Close-up view. The affected area is the front of the torso and arm. The patient is female — 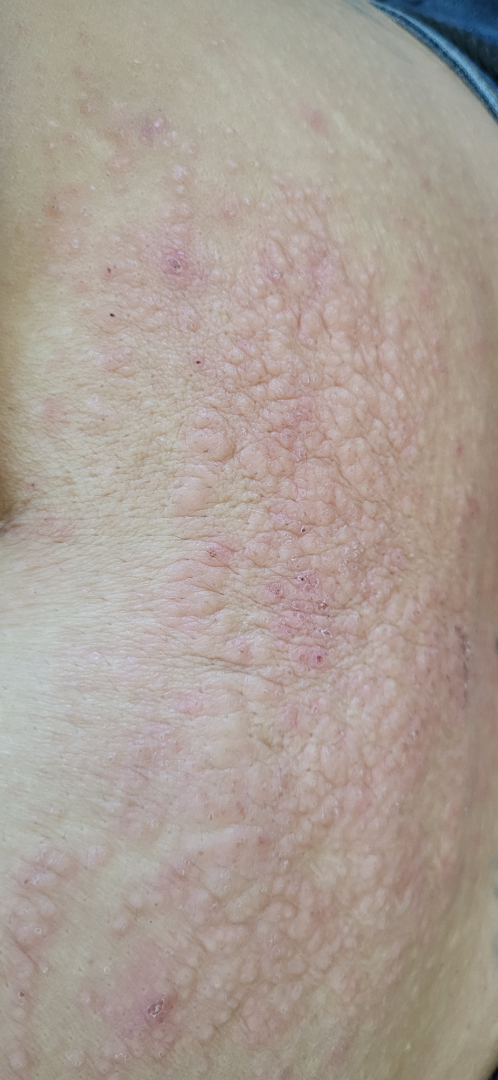<case>
<differential>Lichen Simplex Chronicus</differential>
</case>